A dermoscopic image of a skin lesion; a male patient, aged approximately 85 or older.
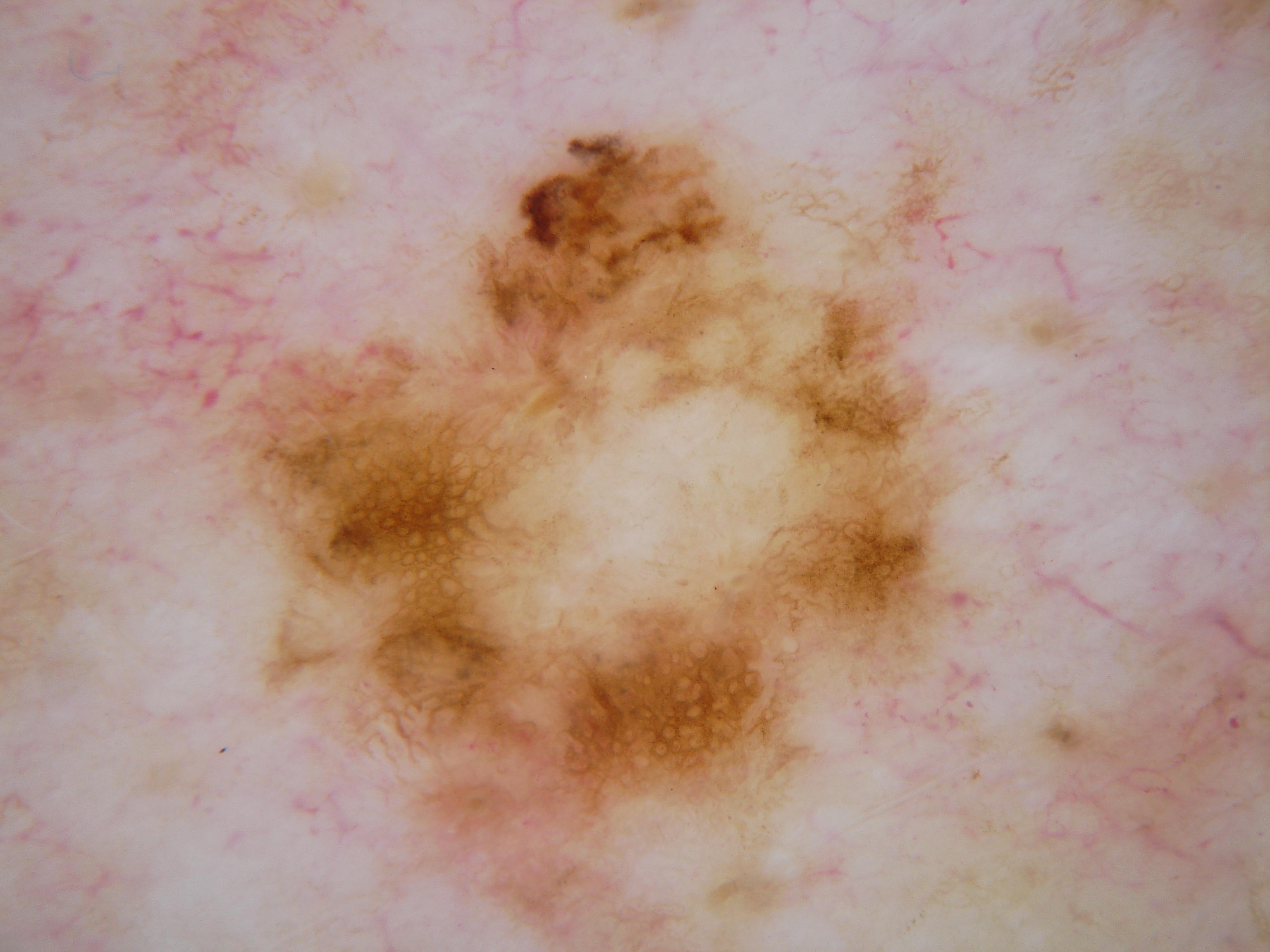Case summary:
With coordinates (x1, y1, x2, y2), the lesion is bounded by 224, 135, 970, 931. Dermoscopically, the lesion shows pigment network.
Diagnosis:
Histopathology confirmed a melanoma, a malignant lesion.